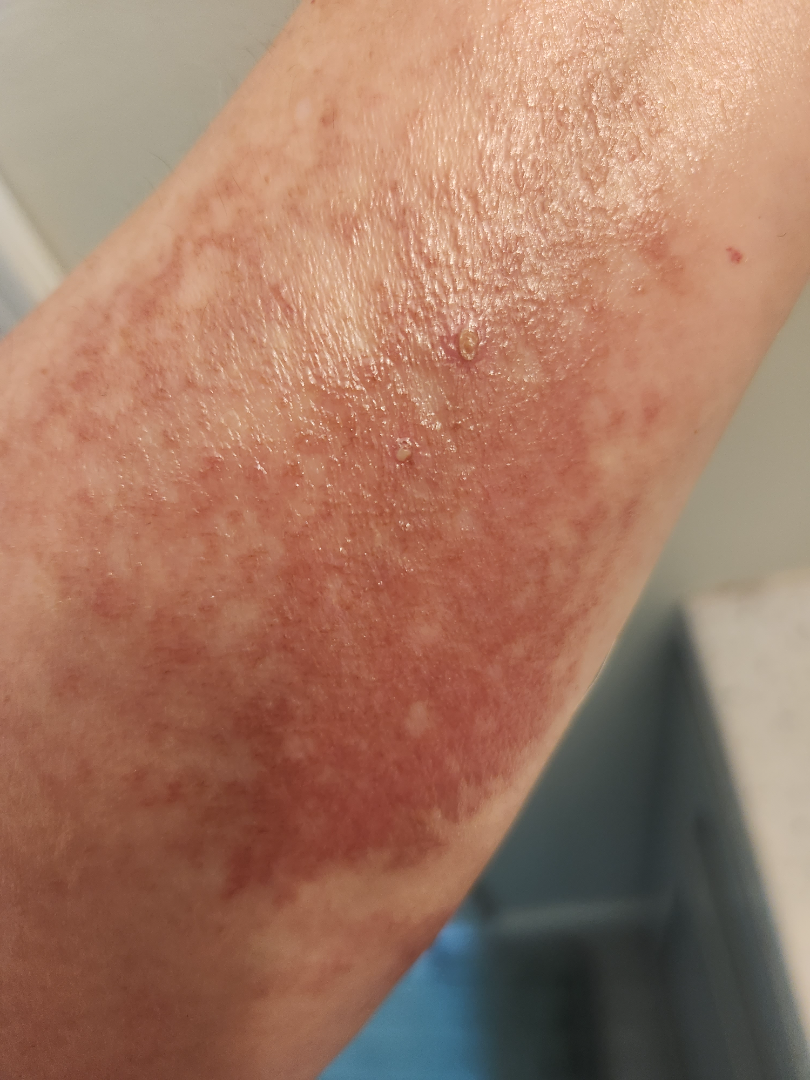The contributor is a female aged 50–59.
Fitzpatrick phototype III.
No relevant systemic symptoms.
The patient described the issue as a rash.
The lesion involves the arm.
Present for one to four weeks.
The photo was captured at an angle.
Texture is reported as rough or flaky and flat.
On photographic review by a dermatologist: most consistent with Allergic Contact Dermatitis; with consideration of Tinea; also raised was Eczema.